The patient reports a history of sunbed use; acquired for a research image collection, with no referral diagnosis; the patient describes having numerous moles; the patient says their skin reddens with sun exposure — 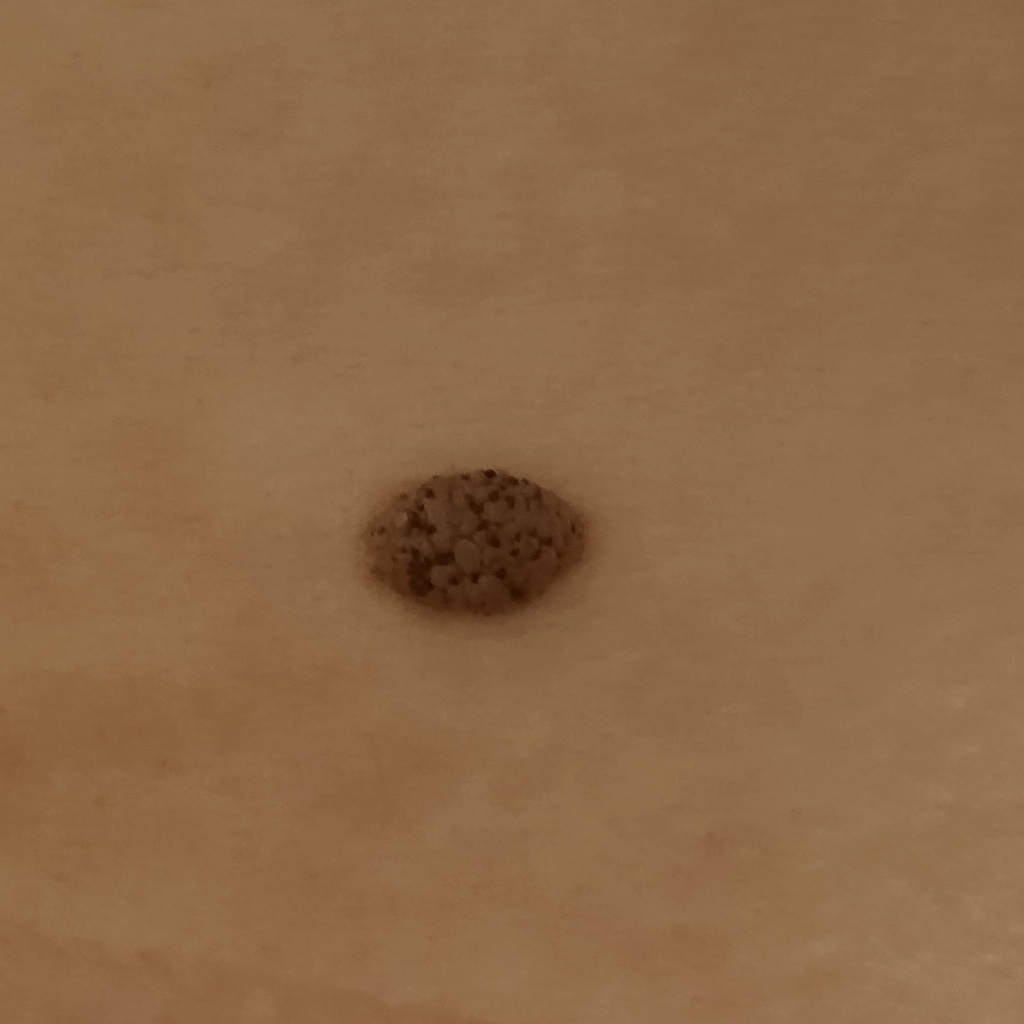Conclusion: The lesion was assessed as a seborrheic keratosis.